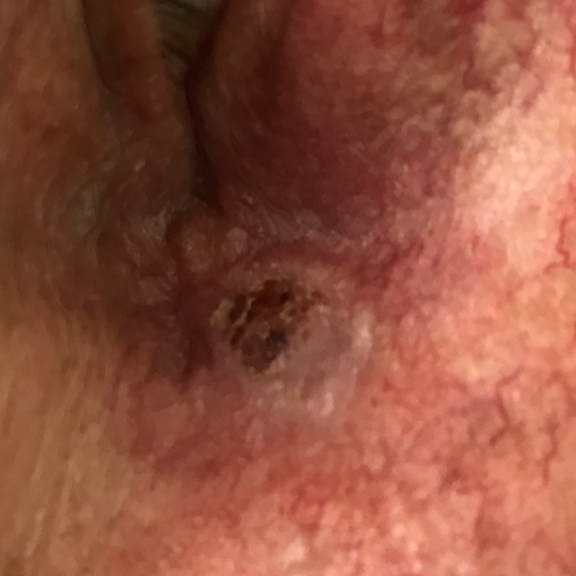– image · smartphone clinical photo
– patient · male, age 65
– exposure history · alcohol use, pesticide exposure, no prior malignancy (patient or family)
– Fitzpatrick · II
– location · the face
– size · 6 × 5 mm
– reported symptoms · itching, pain, elevation, bleeding
– diagnosis · basal cell carcinoma (biopsy-proven)